Dermoscopy of a skin lesion: 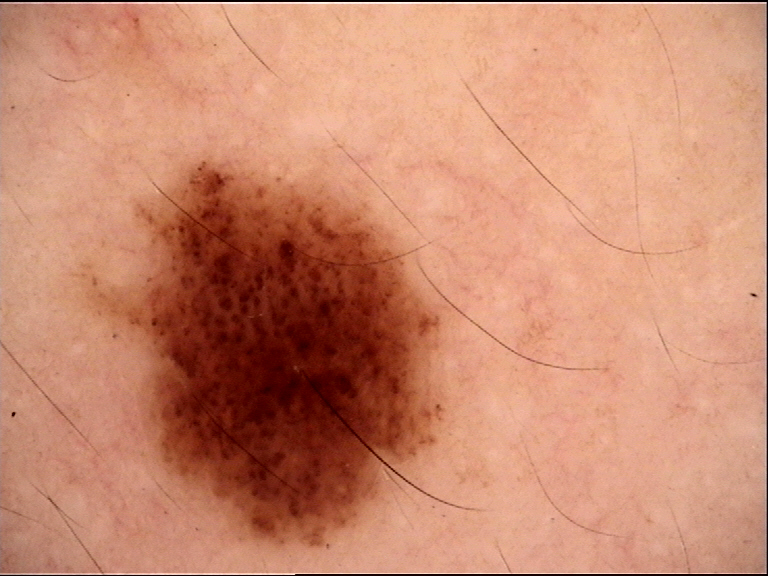The architecture is that of a banal lesion. The diagnostic label was a compound nevus.